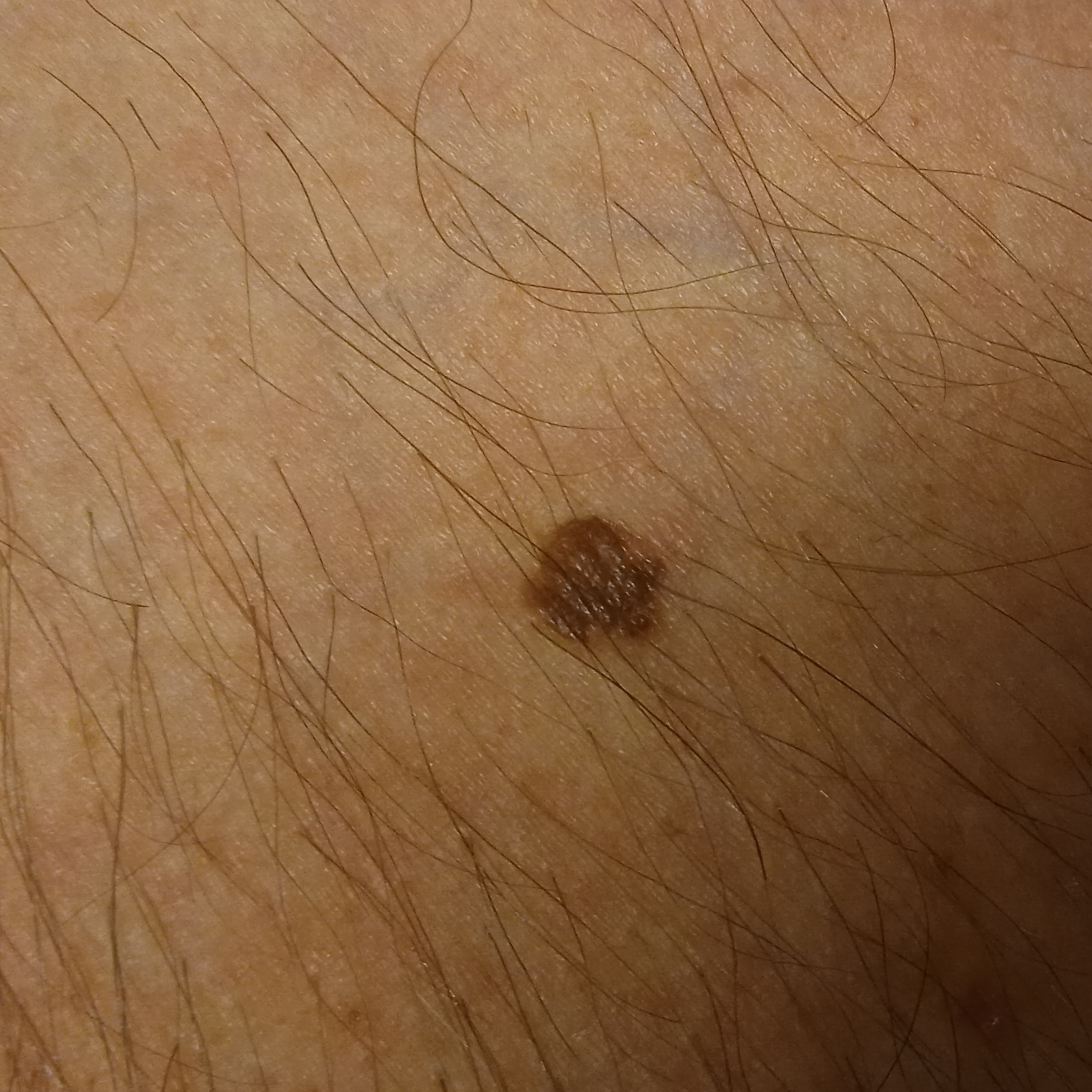Imaged for a research study, with no referral diagnosis recorded.
The patient says their skin reddens painfully with sun exposure.
A clinical close-up of a skin lesion.
Located on an arm.
The lesion is about 5.5 mm across.
The diagnostic impression was a melanocytic nevus.